By history, pesticide exposure and alcohol use · a male subject aged 73 · Fitzpatrick phototype II · a clinical close-up photograph of a skin lesion:
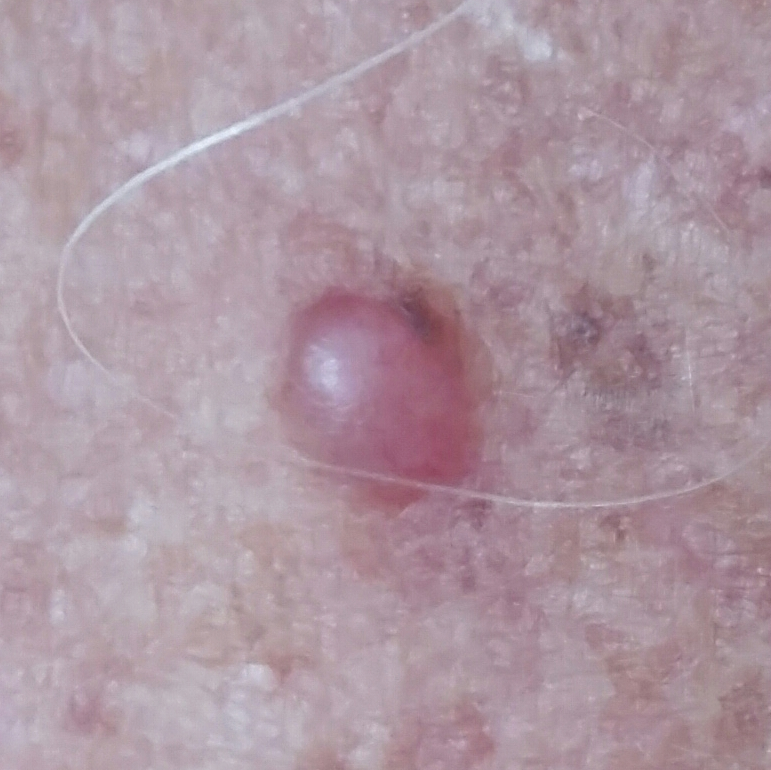The lesion is on the chest.
Measuring about 5 × 3 mm.
By the patient's account, the lesion is elevated and itches.
Histopathologically confirmed as a basal cell carcinoma.